A dermoscopic image of a skin lesion.
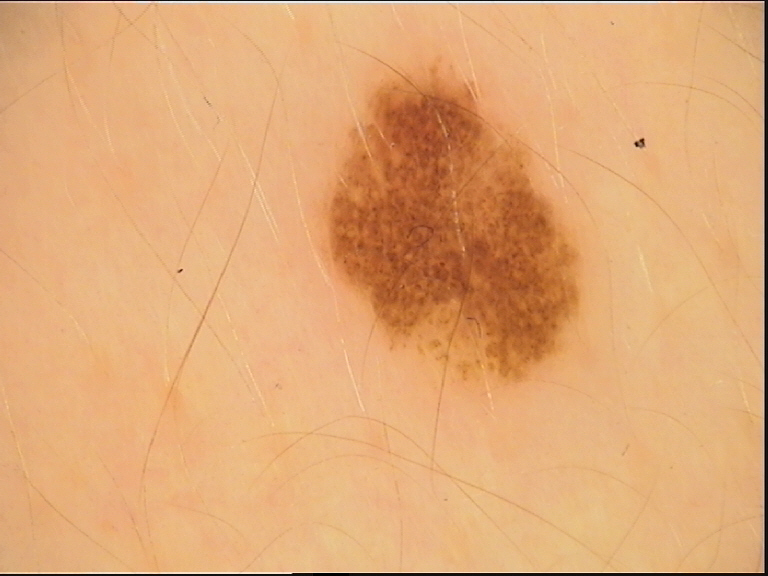Diagnosed as a benign lesion — a dysplastic compound nevus.